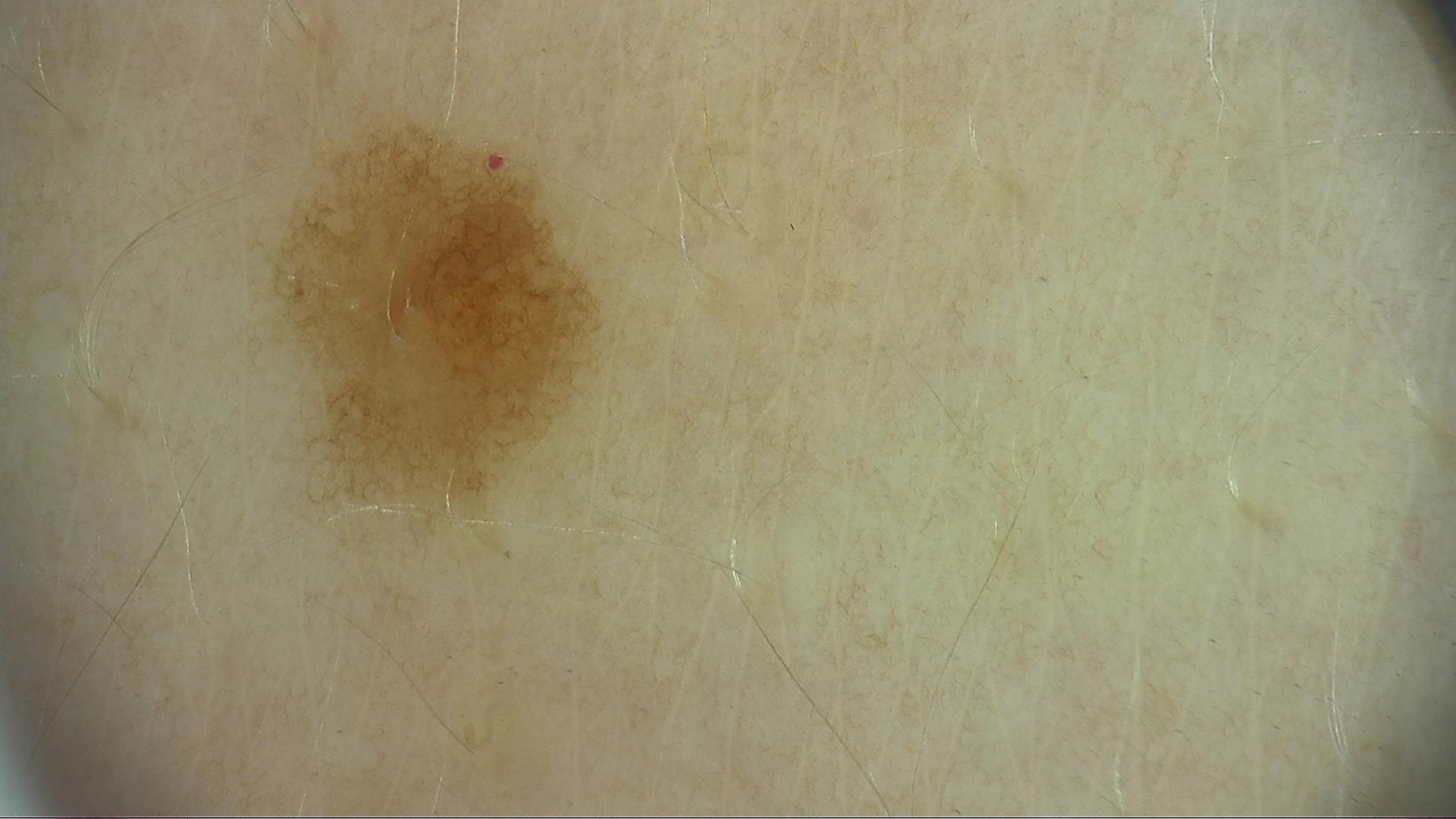Impression:
Consistent with a dysplastic junctional nevus.